A dermoscopic view of a skin lesion: 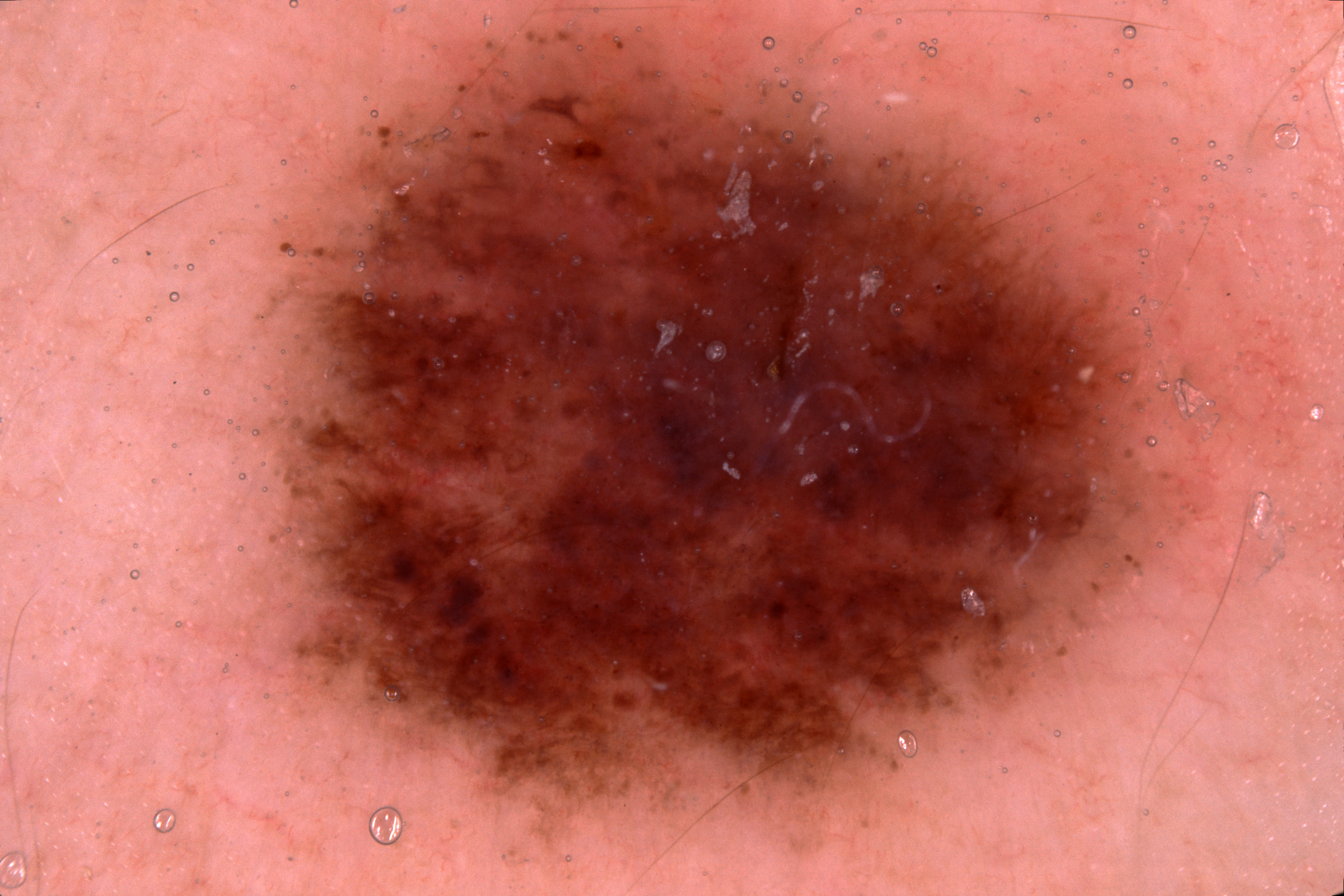Case summary:
As (left, top, right, bottom), the lesion is located at <bbox>248, 0, 1253, 857</bbox>. The lesion takes up about 50% of the image. Part of the lesion extends beyond the imaged area. Dermoscopic assessment notes pigment network.
Conclusion:
The lesion was assessed as a melanocytic nevus, a benign lesion.